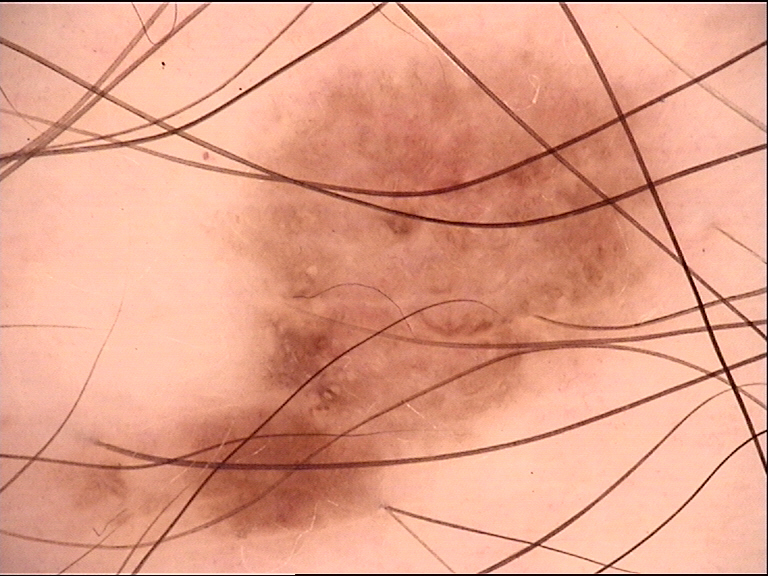assessment = dysplastic junctional nevus (expert consensus).